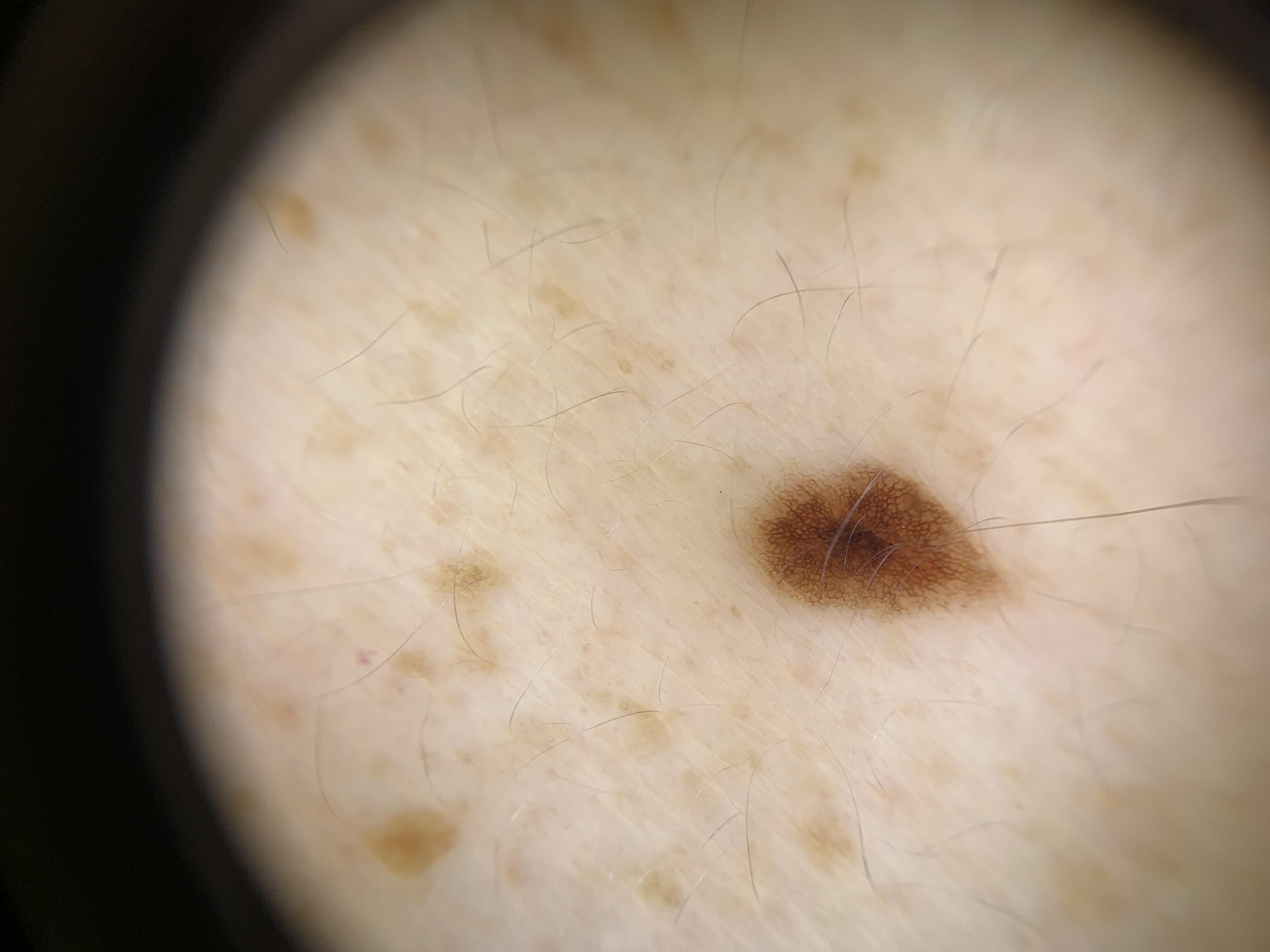{
  "image": "dermoscopy",
  "patient": {
    "age_approx": 70,
    "sex": "female"
  },
  "skin_type": "I",
  "lesion_location": {
    "region": "the trunk",
    "detail": "the posterior trunk"
  },
  "diagnosis": {
    "name": "Nevus",
    "malignancy": "benign",
    "confirmation": "expert clinical impression",
    "lineage": "melanocytic"
  }
}